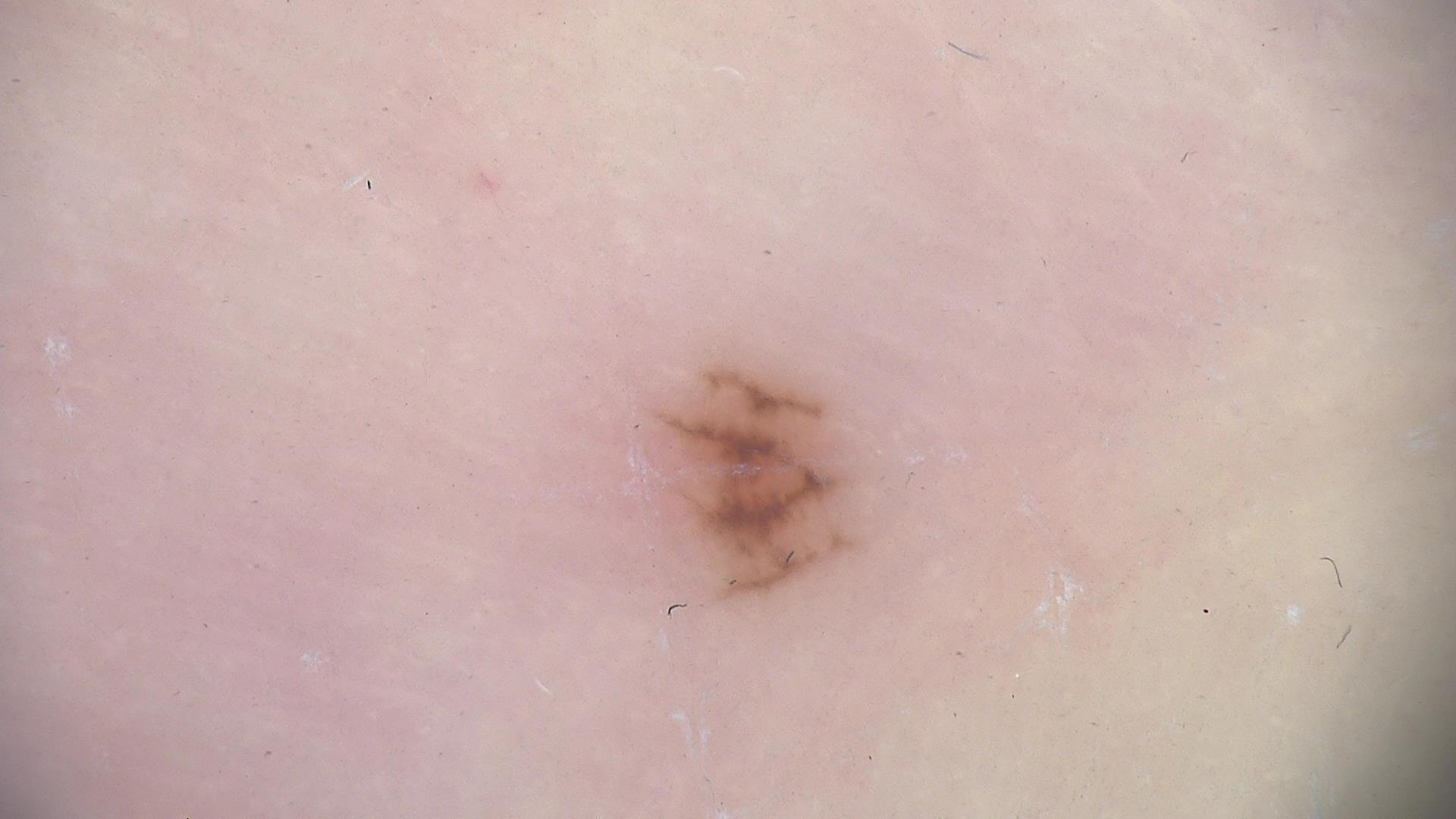{"diagnosis": {"name": "acral dysplastic junctional nevus", "code": "ajd", "malignancy": "benign", "super_class": "melanocytic", "confirmation": "expert consensus"}}